Male subject, age 18–29; the lesion is associated with bothersome appearance and enlargement; close-up view; the patient reported no systemic symptoms:
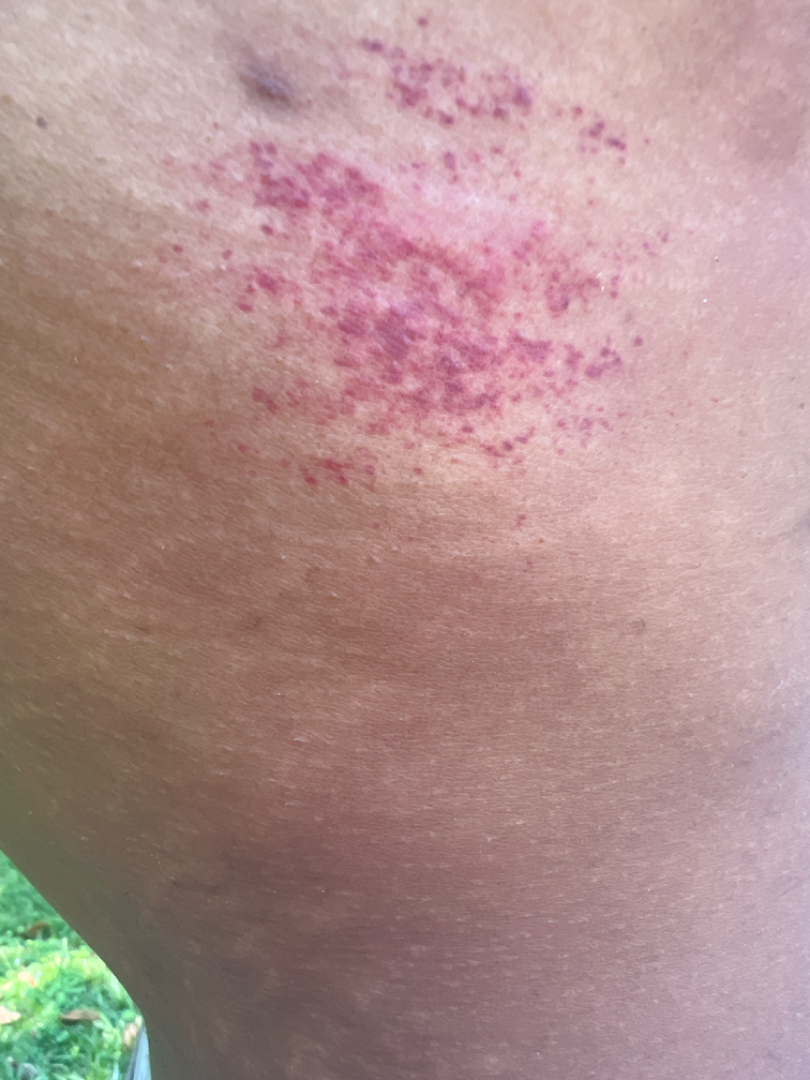On remote dermatologist review, Leukocytoclastic Vasculitis and Purpura were considered with similar weight.